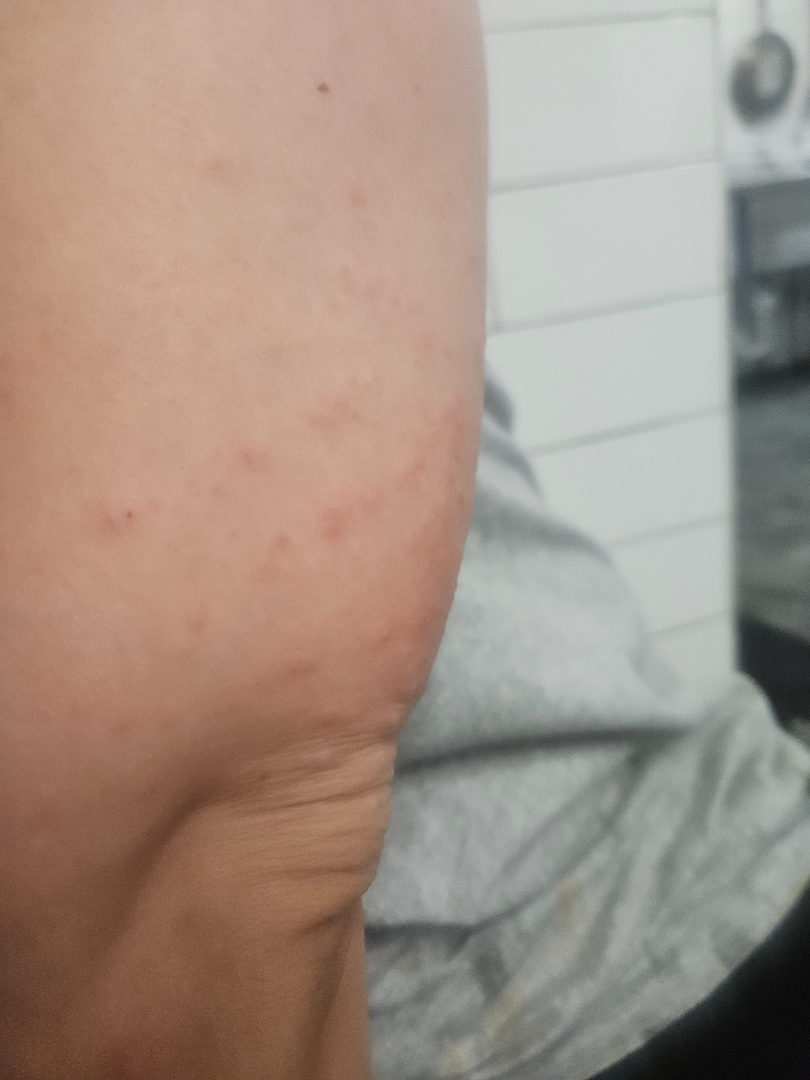The skin condition could not be confidently assessed from this image.